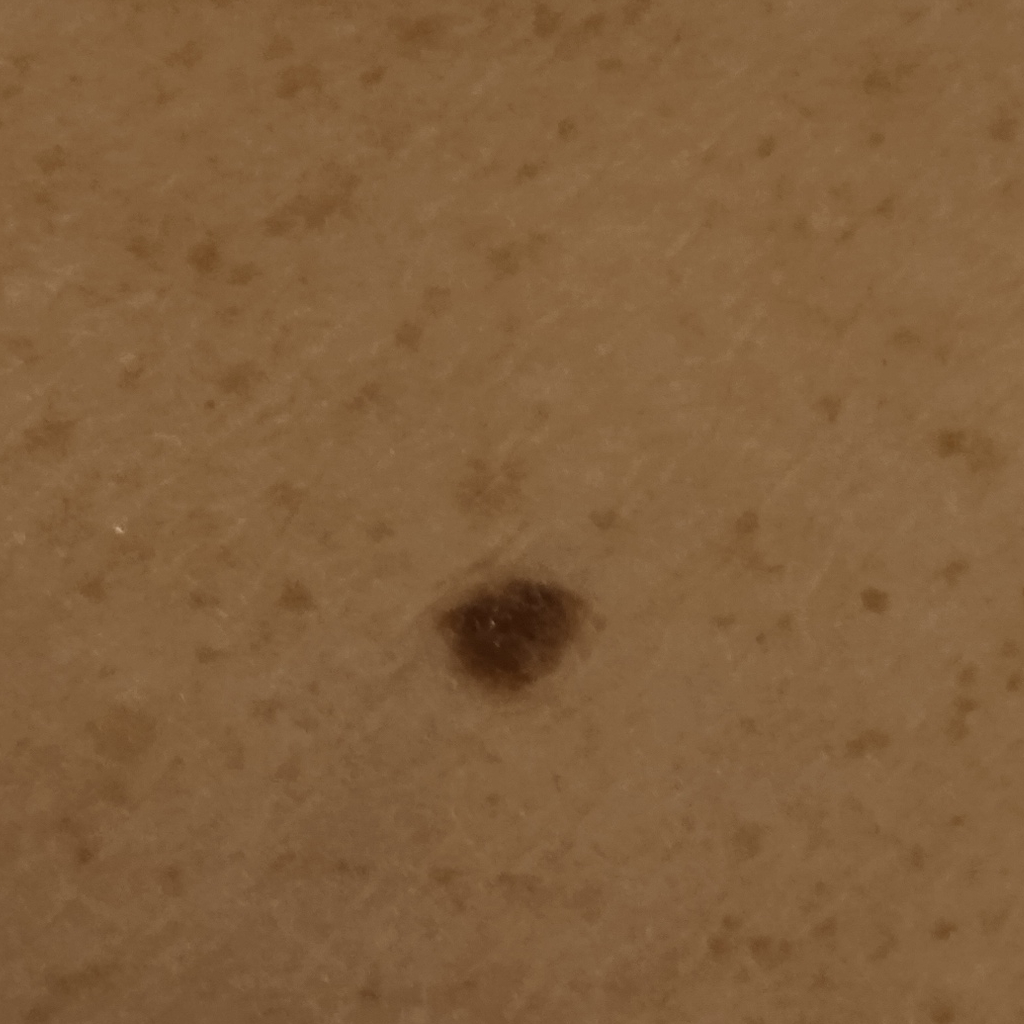sun reaction = skin reddens with sun exposure; risk factors = a personal history of cancer, no immunosuppression, no family history of skin cancer; referral = research study (no referral diagnosis); modality = clinical photo; patient = male, aged 72; nevus count = few melanocytic nevi overall; body site = the back; lesion size = 5.6 mm; assessment = melanocytic nevus (dermatologist consensus).